The patient described the issue as a rash, the lesion is described as raised or bumpy, the condition has been present for less than one week, this is a close-up image, the affected area is the head or neck, the lesion is associated with itching: 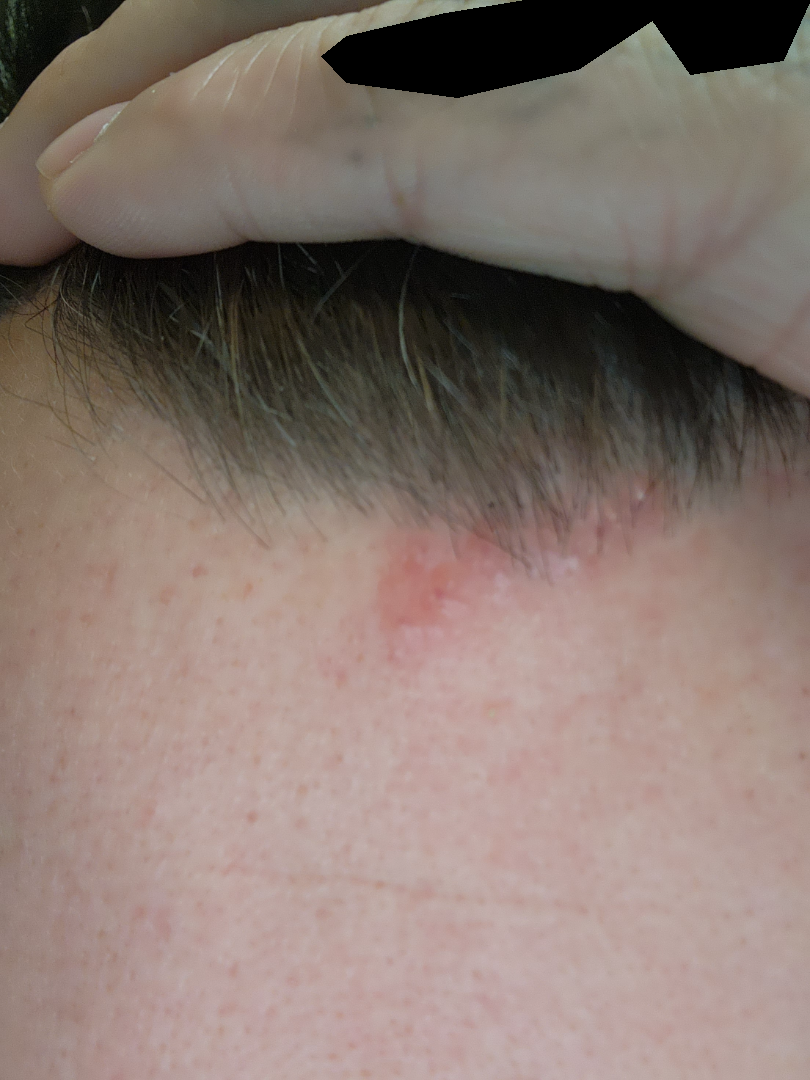The dermatologist could not determine a likely condition from the photograph alone.